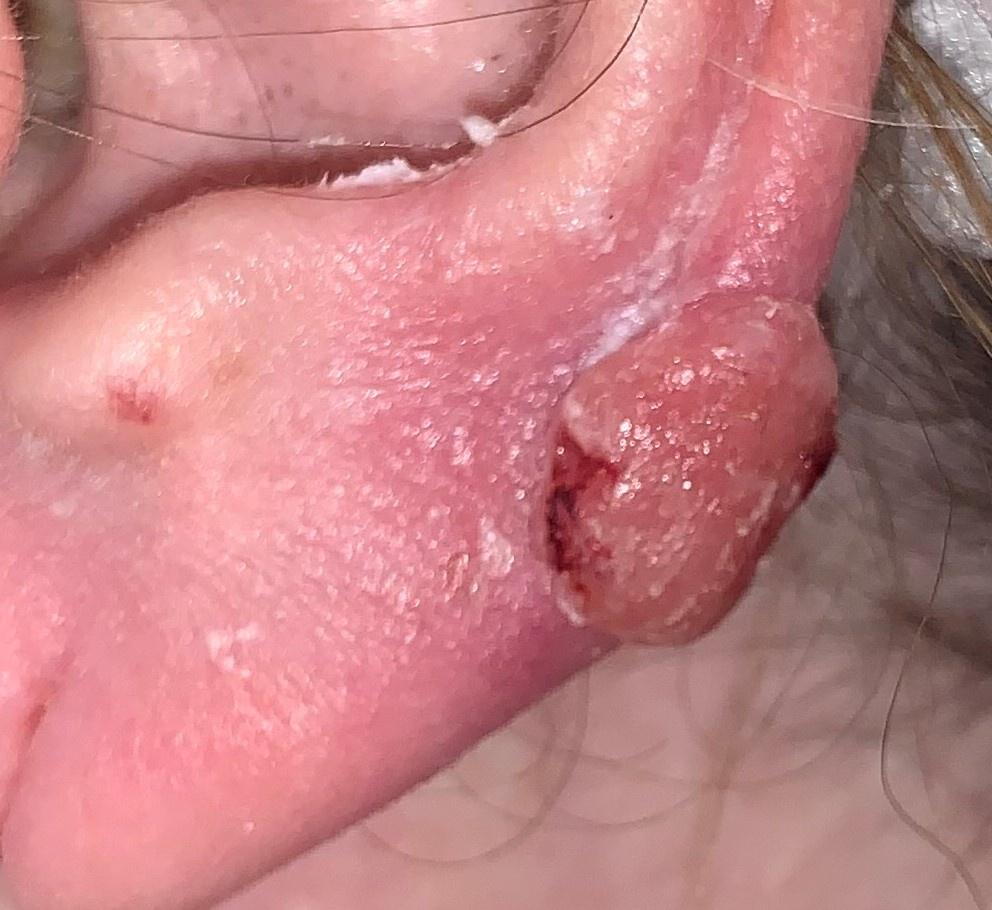patient: female, aged around 65; skin type: II; body site: the head or neck; diagnosis: Squamous cell carcinoma (biopsy-proven).